A dermoscopic close-up of a skin lesion: 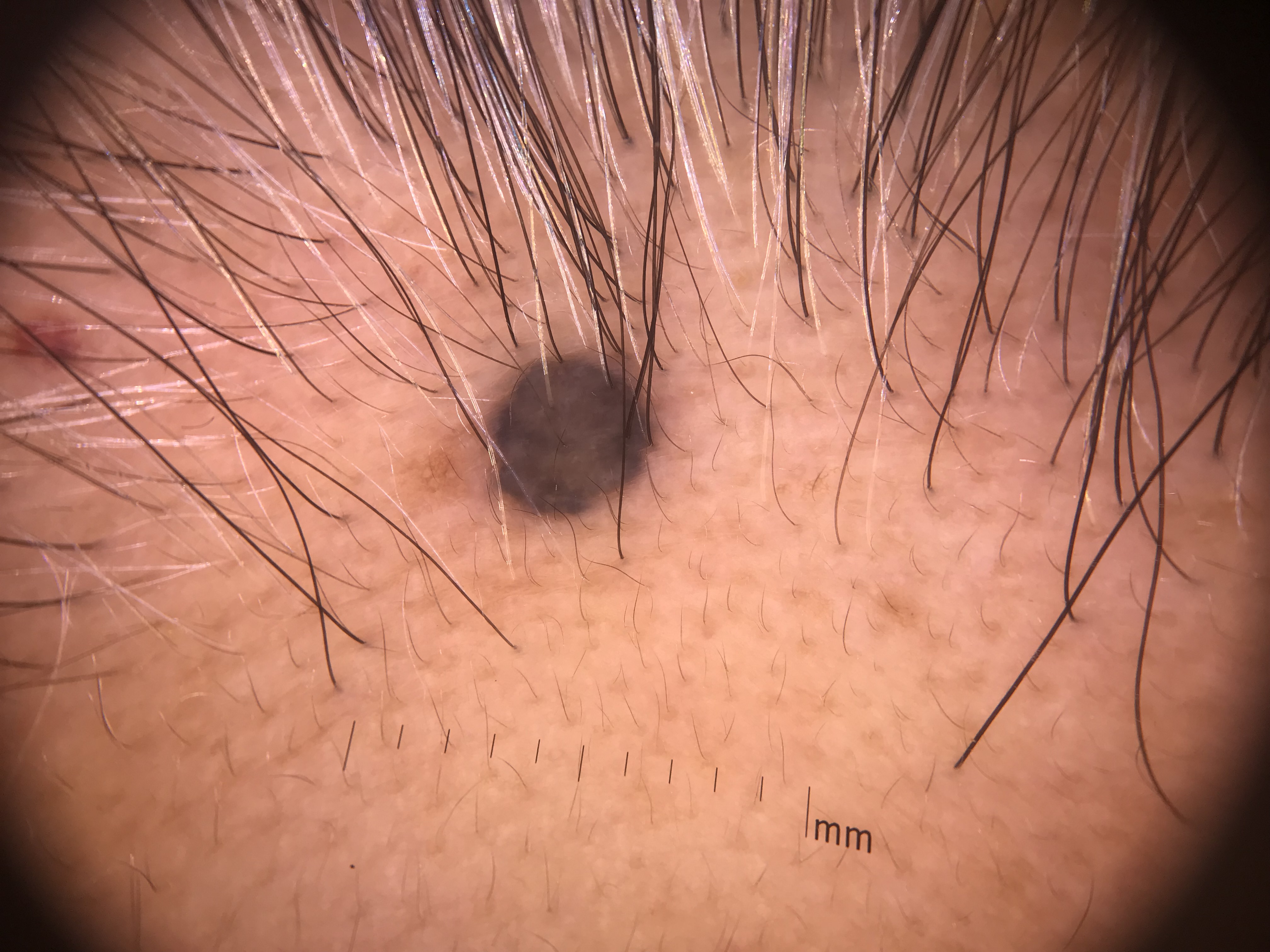<dermoscopy>
  <lesion_type>
    <main_class>banal</main_class>
    <pattern>dermal</pattern>
  </lesion_type>
  <diagnosis>
    <name>blue nevus</name>
    <code>bdb</code>
    <malignancy>benign</malignancy>
    <super_class>melanocytic</super_class>
    <confirmation>expert consensus</confirmation>
  </diagnosis>
</dermoscopy>